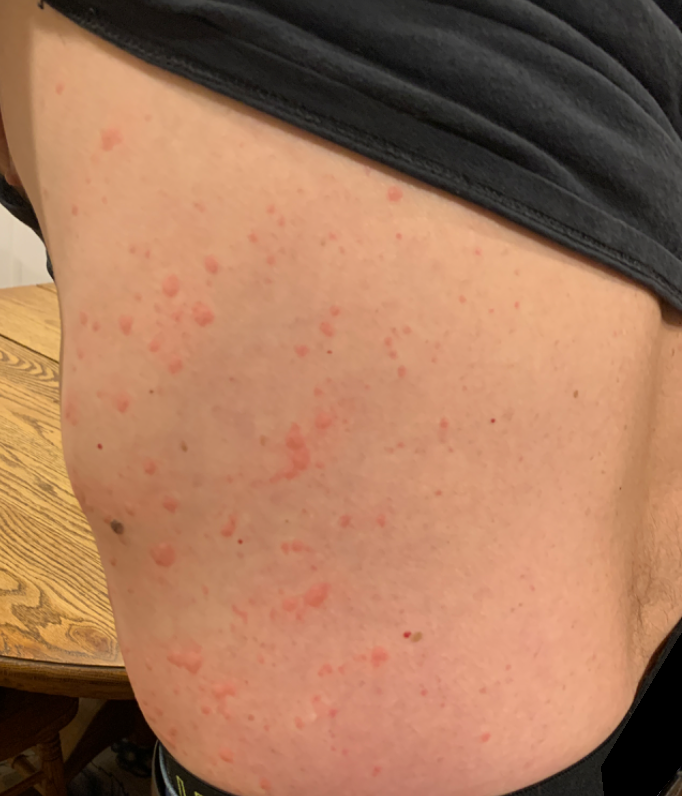Located on the front of the torso. Male contributor, age 60–69. An image taken at an angle. On remote review of the image: the impression on review was Urticaria.